A dermoscopic close-up of a skin lesion:
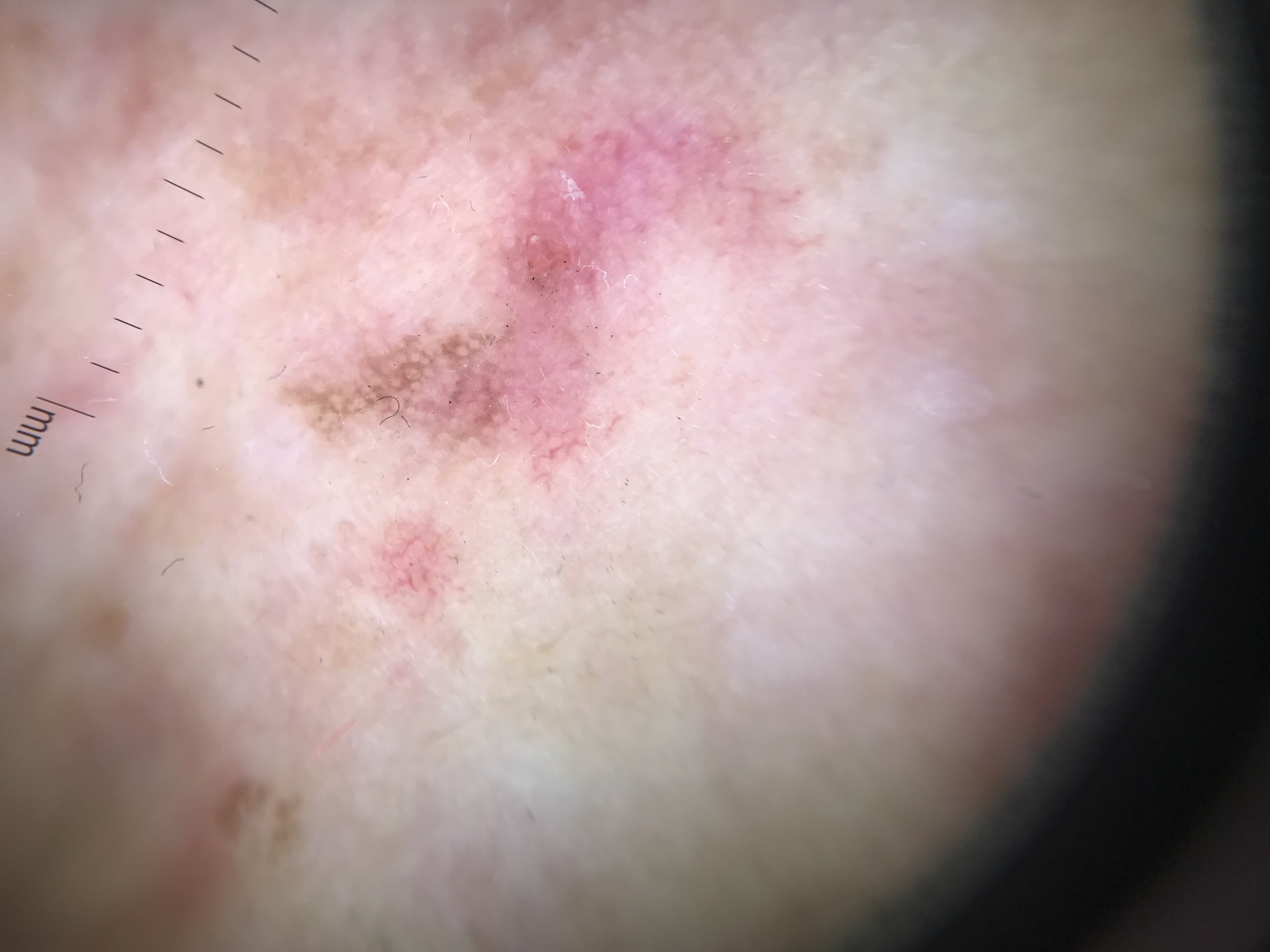Q: What is the lesion category?
A: keratinocytic
Q: What was the diagnostic impression?
A: seborrheic keratosis (expert consensus)